An image taken at a distance:
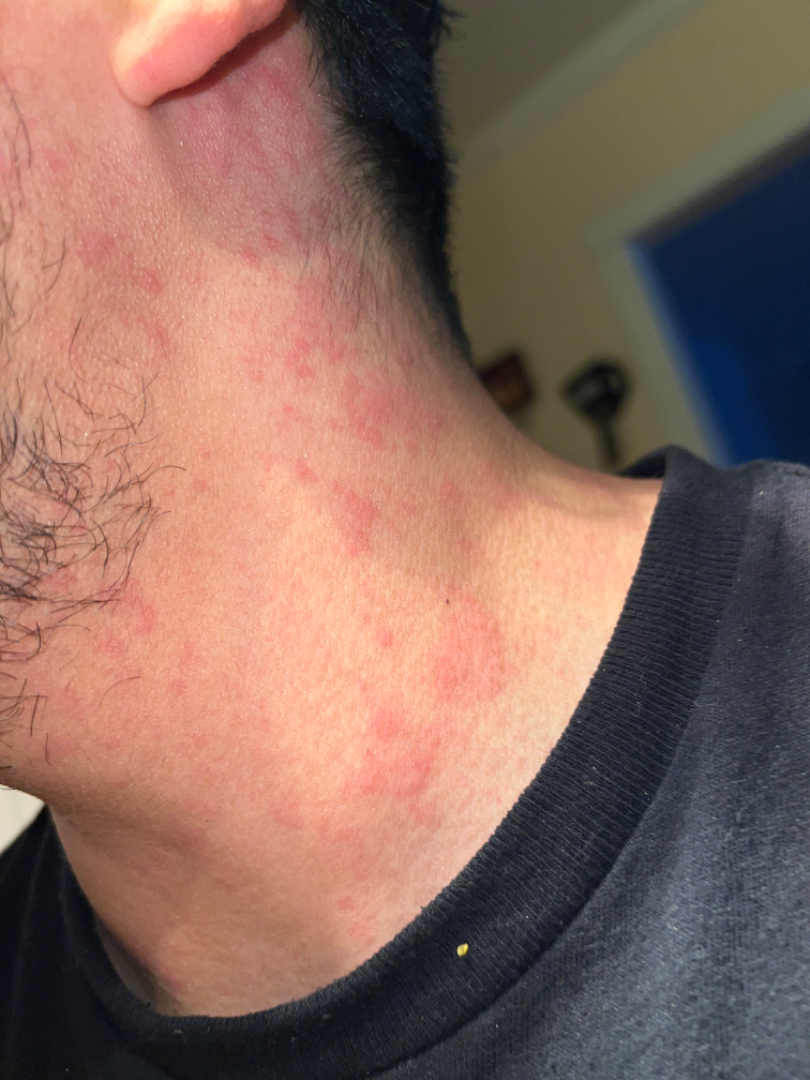clinical impression = Urticaria and Allergic Contact Dermatitis were each considered, in no particular order; a remote consideration is Drug Rash.